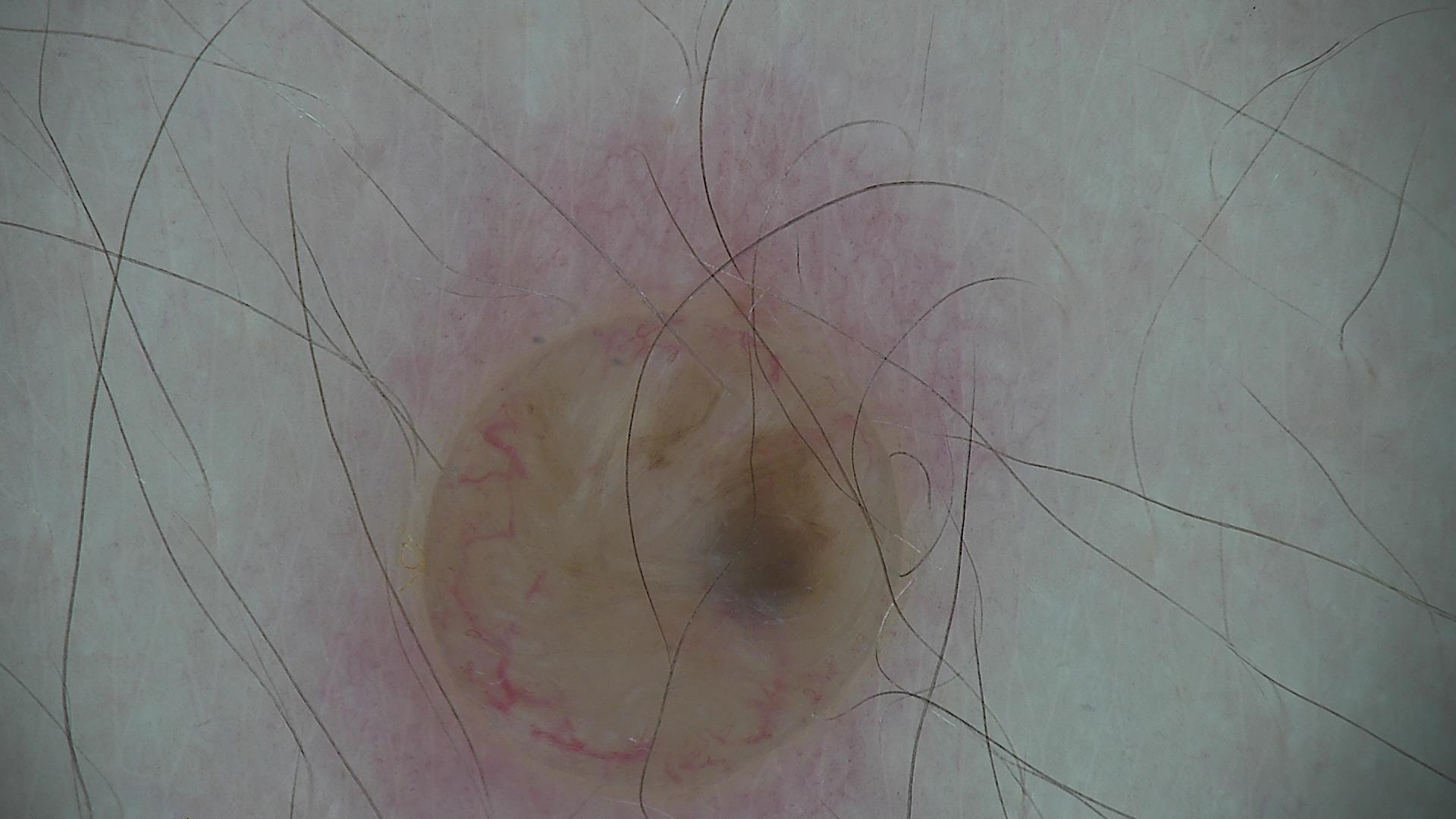Case:
- modality · dermatoscopy
- label · dermal nevus (expert consensus)